A dermoscopic photograph of a skin lesion.
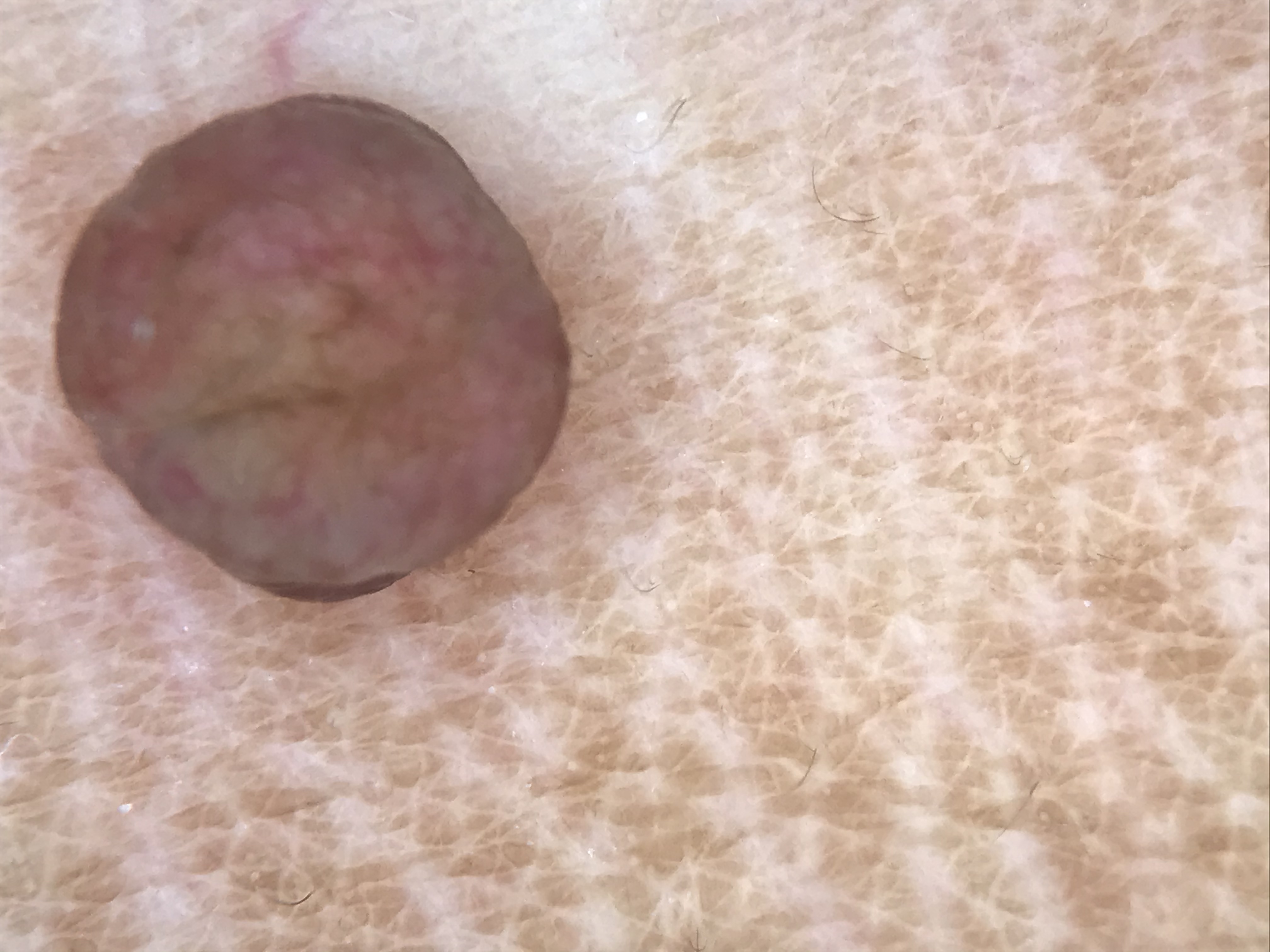Impression: The diagnosis was a banal lesion — a dermal nevus.